A dermatoscopic image of a skin lesion, the subject is a male aged around 50: 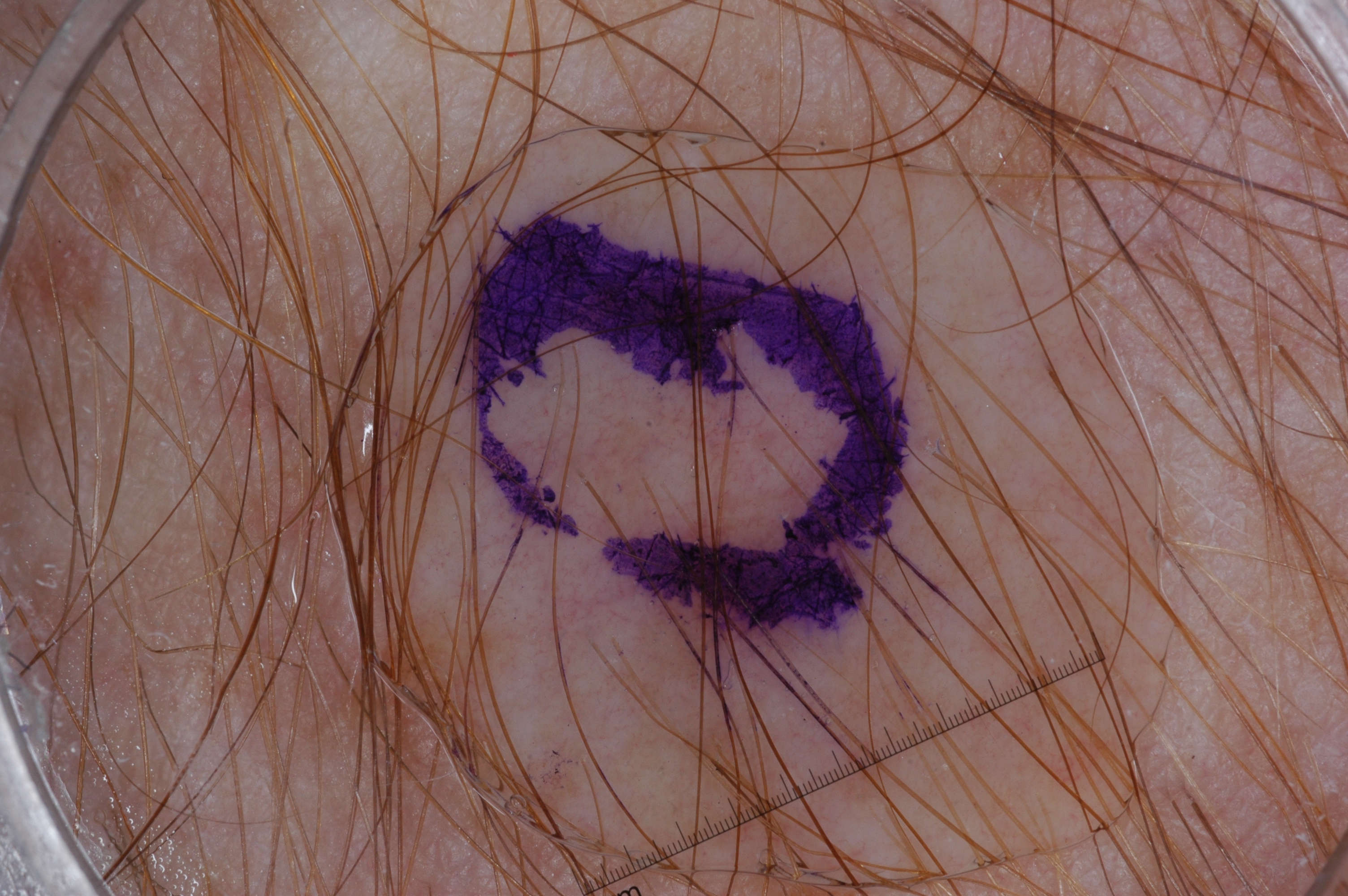In (x1, y1, x2, y2) order, the visible lesion spans (457, 183, 975, 701). On dermoscopy, the lesion shows no pigment network, negative network, streaks, or milia-like cysts. Consistent with a seborrheic keratosis.